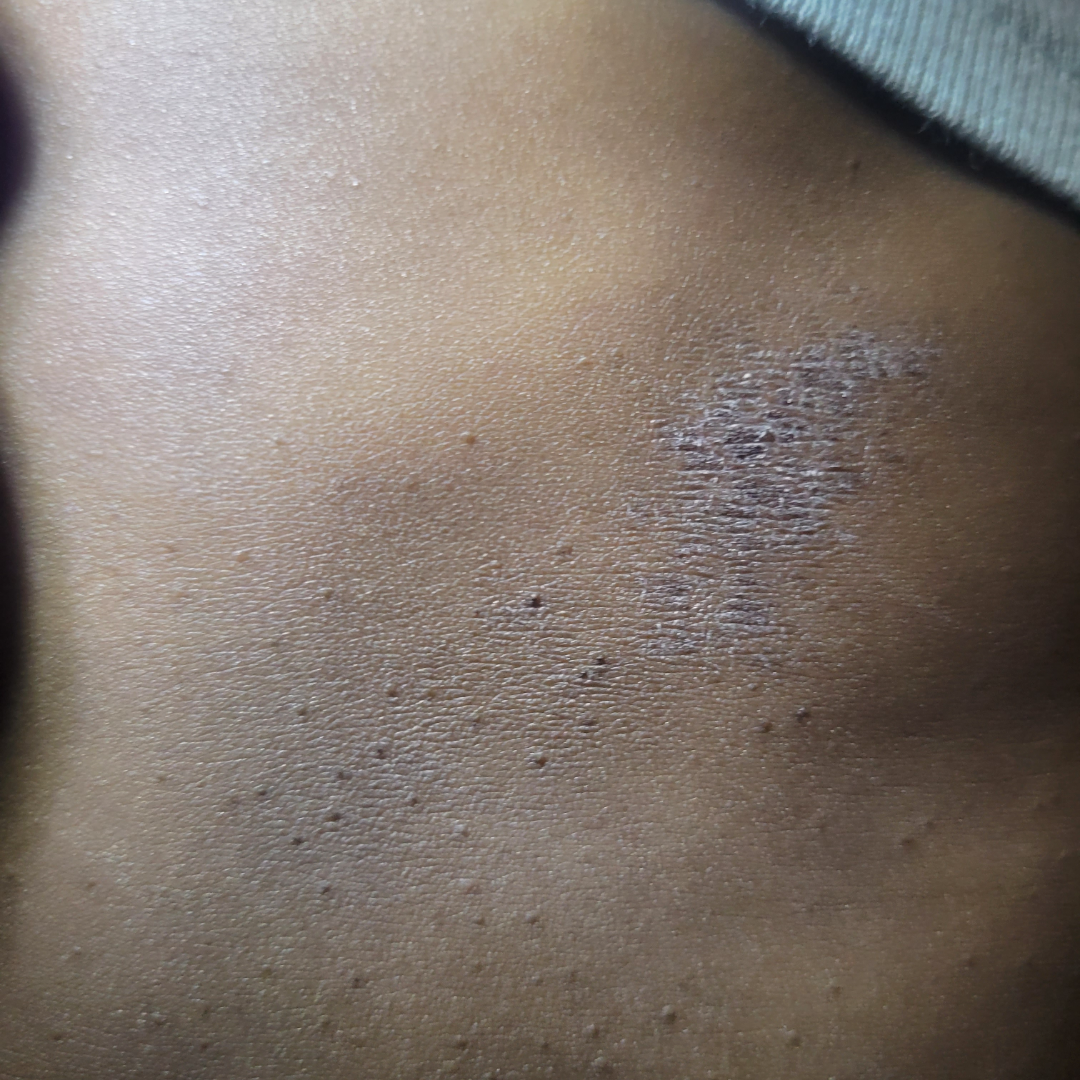The affected area is the front of the torso. A close-up photograph. The differential, in no particular order, includes Psoriasis and Lichen Simplex Chronicus.